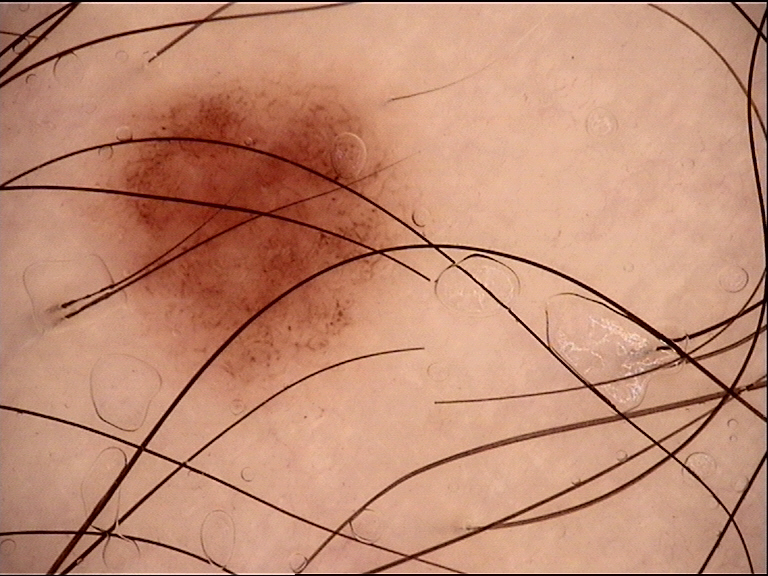A dermoscopic photograph of a skin lesion. The diagnostic label was a dysplastic junctional nevus.